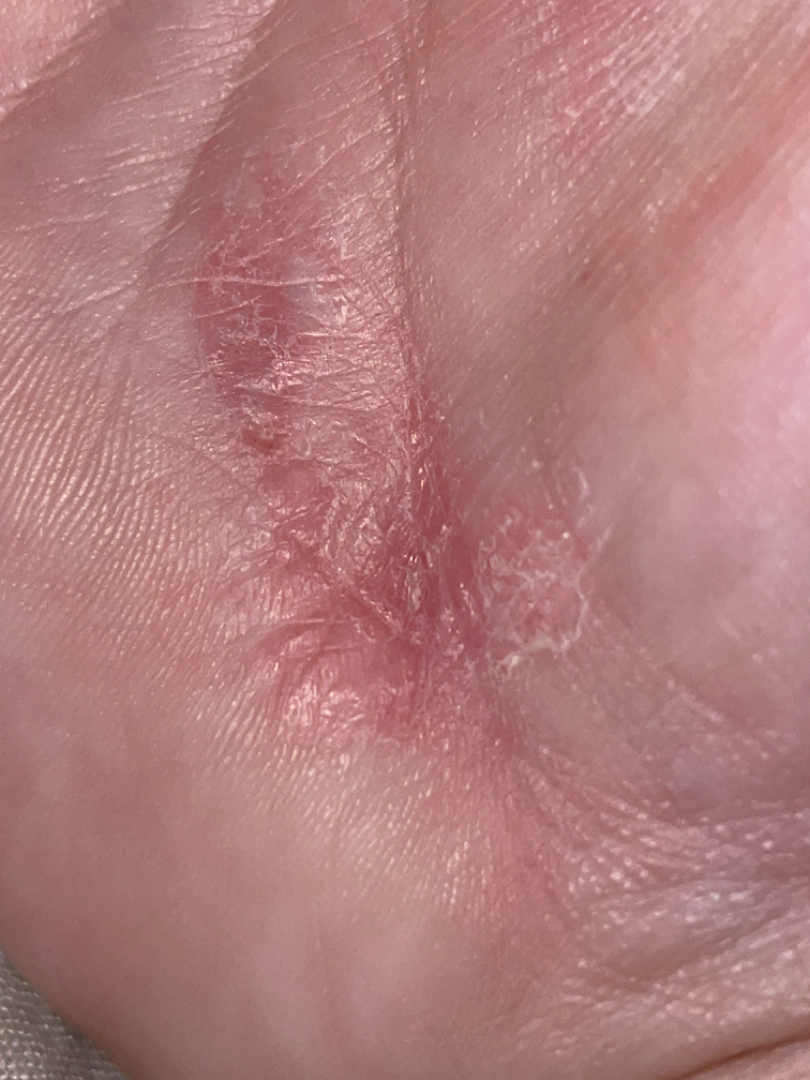The photo was captured at an angle. The condition has been present for three to twelve months. The contributor reports the lesion is rough or flaky. The lesion involves the palm. On photographic review by a dermatologist, the impression was split between Psoriasis, Eczema and Allergic Contact Dermatitis.